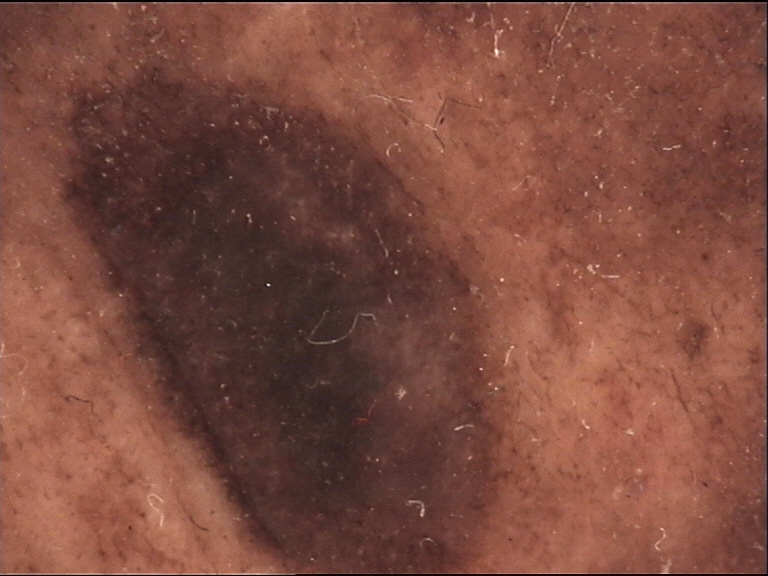A skin lesion imaged with a dermatoscope. The architecture is that of a banal lesion. Consistent with a congenital compound nevus.